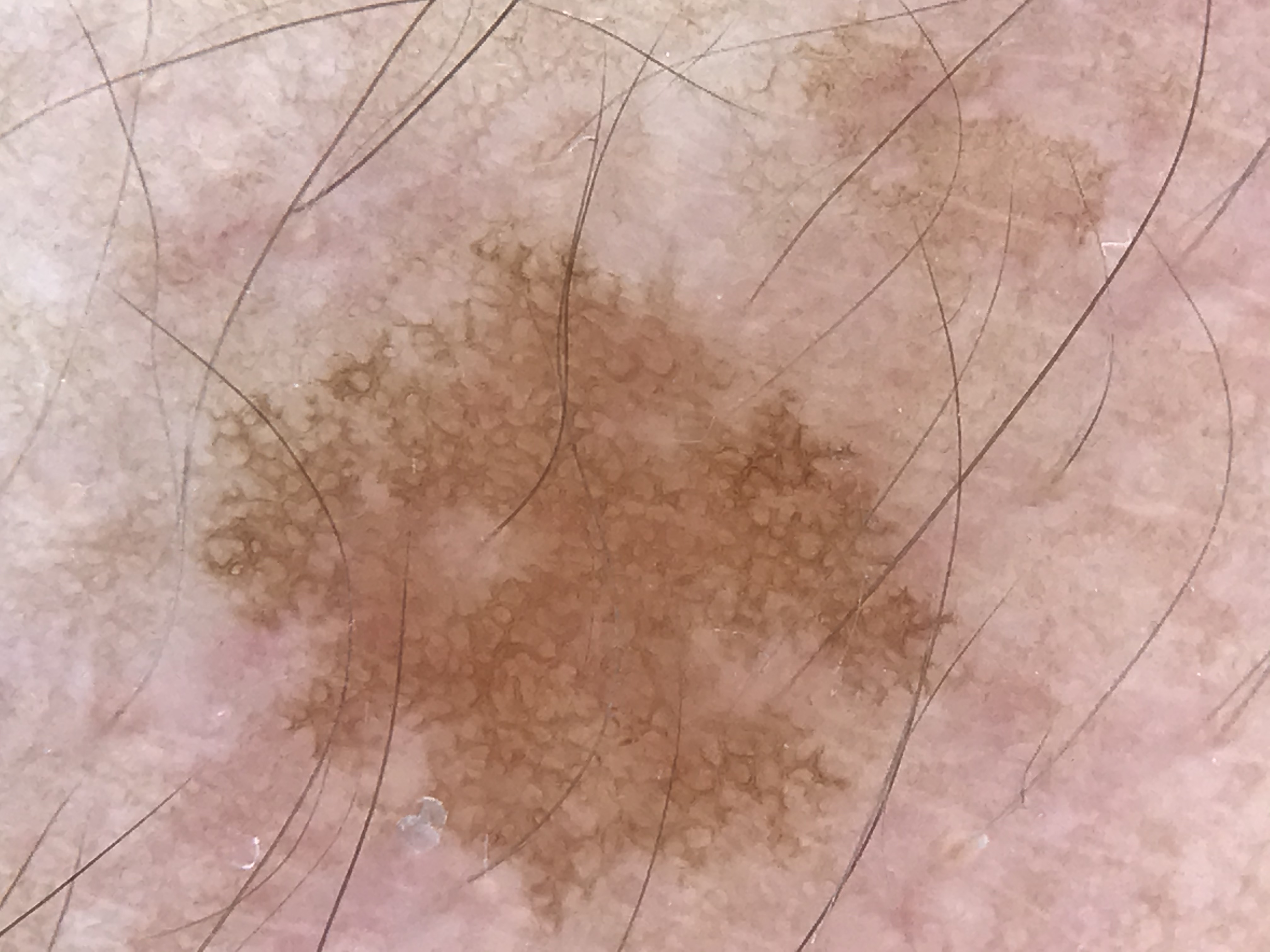Q: What is the imaging modality?
A: dermatoscopy
Q: What was the diagnostic impression?
A: solar lentigo (expert consensus)